A dermoscopic image of a skin lesion.
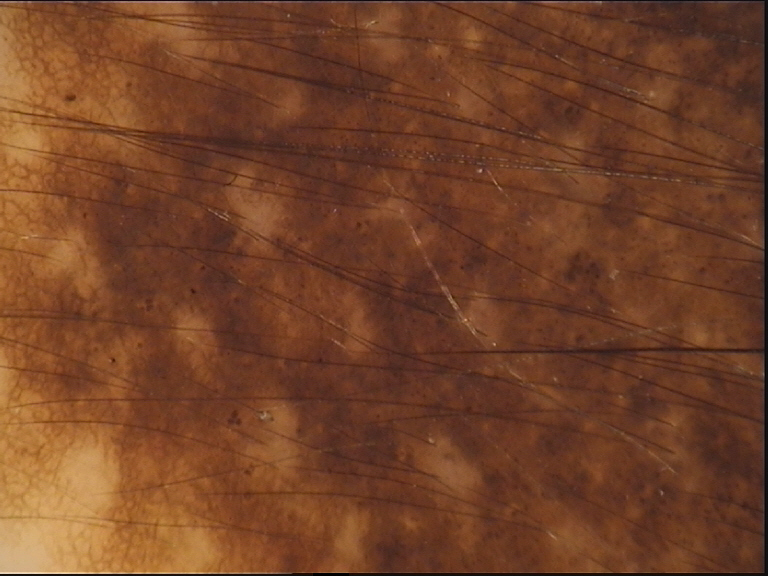This is a banal lesion. The diagnostic label was a congenital compound nevus.